A dermoscopic photograph of a skin lesion: 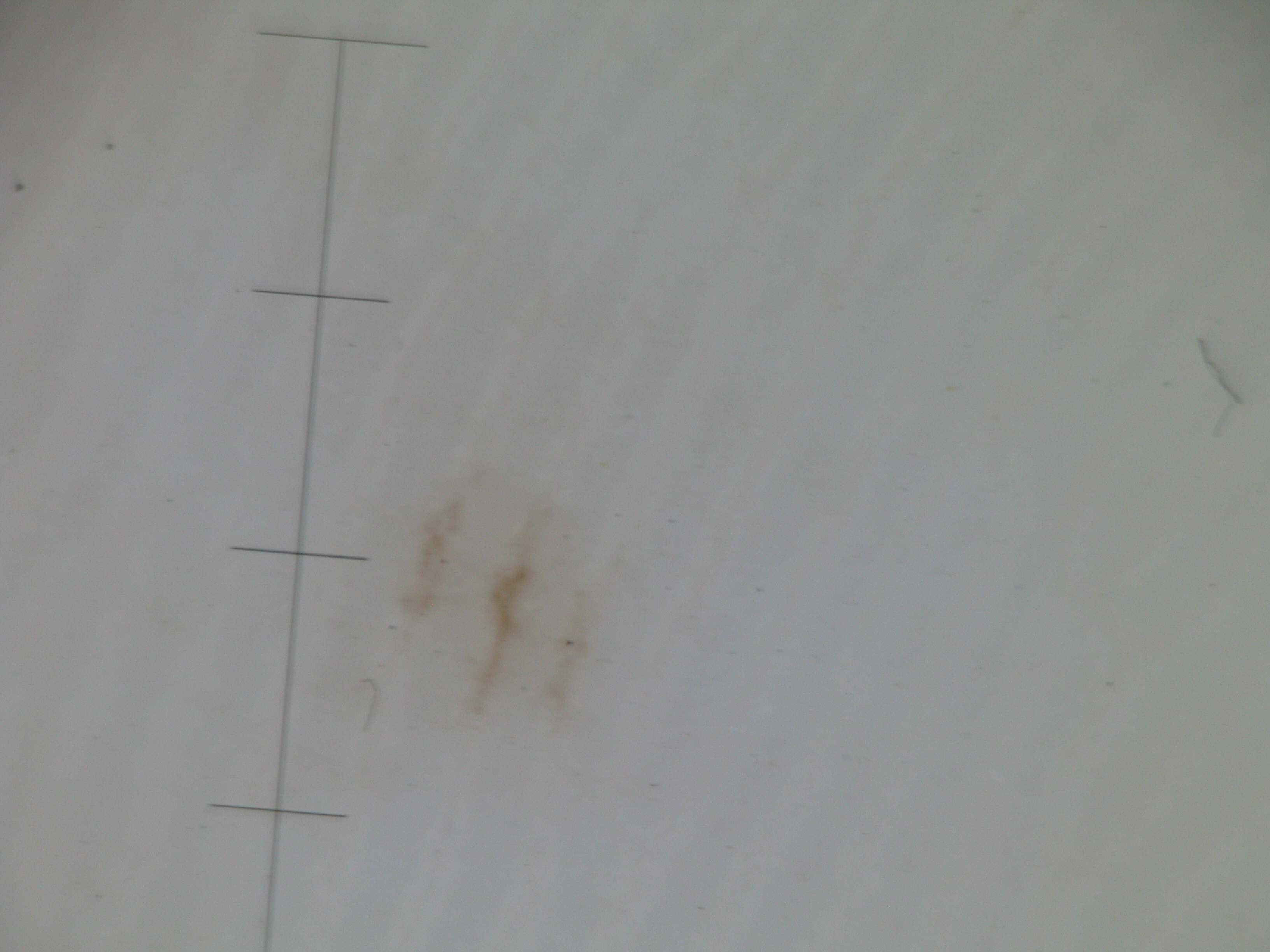<case>
<diagnosis>
<name>acral junctional nevus</name>
<code>ajb</code>
<malignancy>benign</malignancy>
<super_class>melanocytic</super_class>
<confirmation>expert consensus</confirmation>
</diagnosis>
</case>